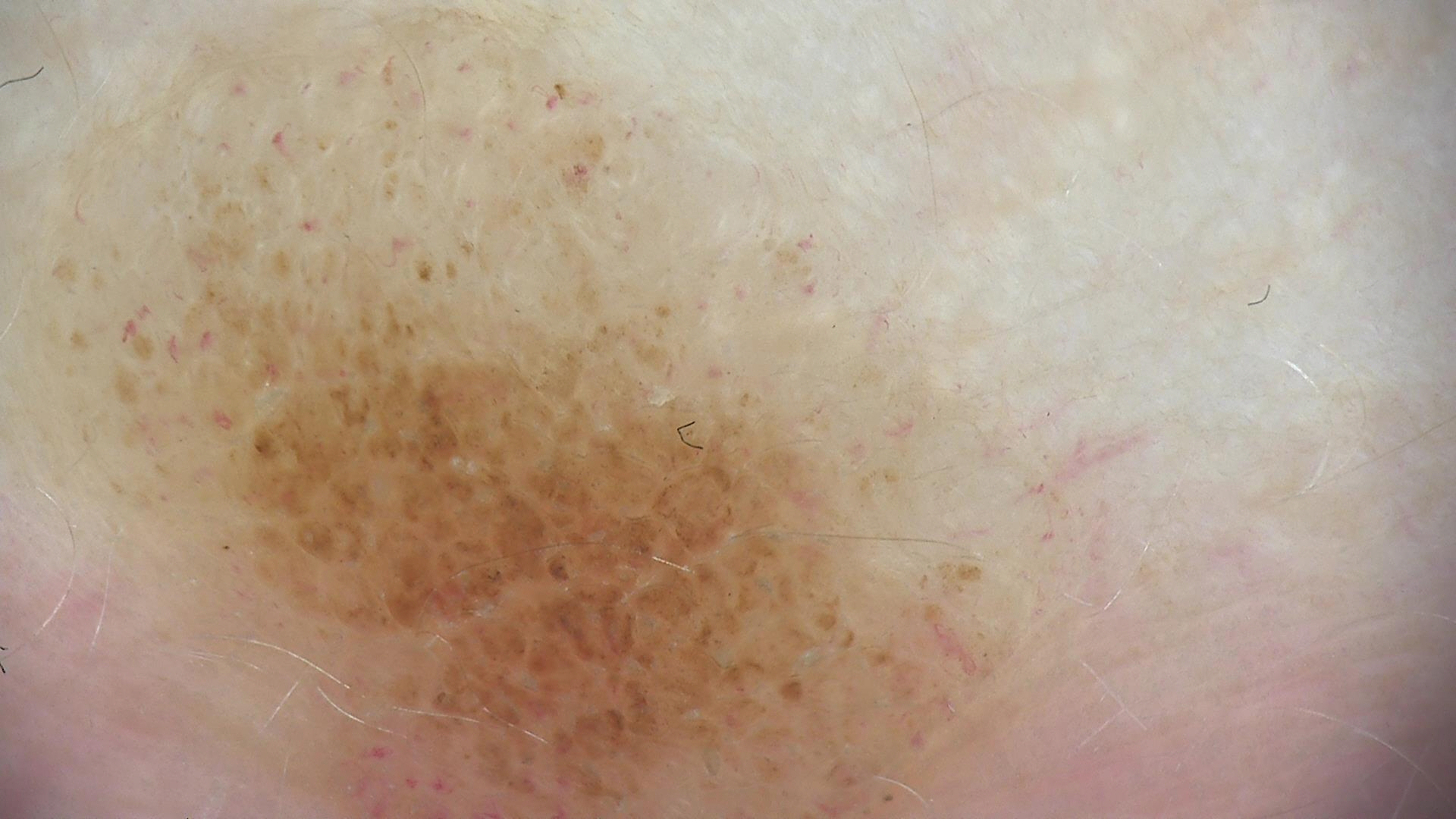Case:
- class — compound nevus (expert consensus)